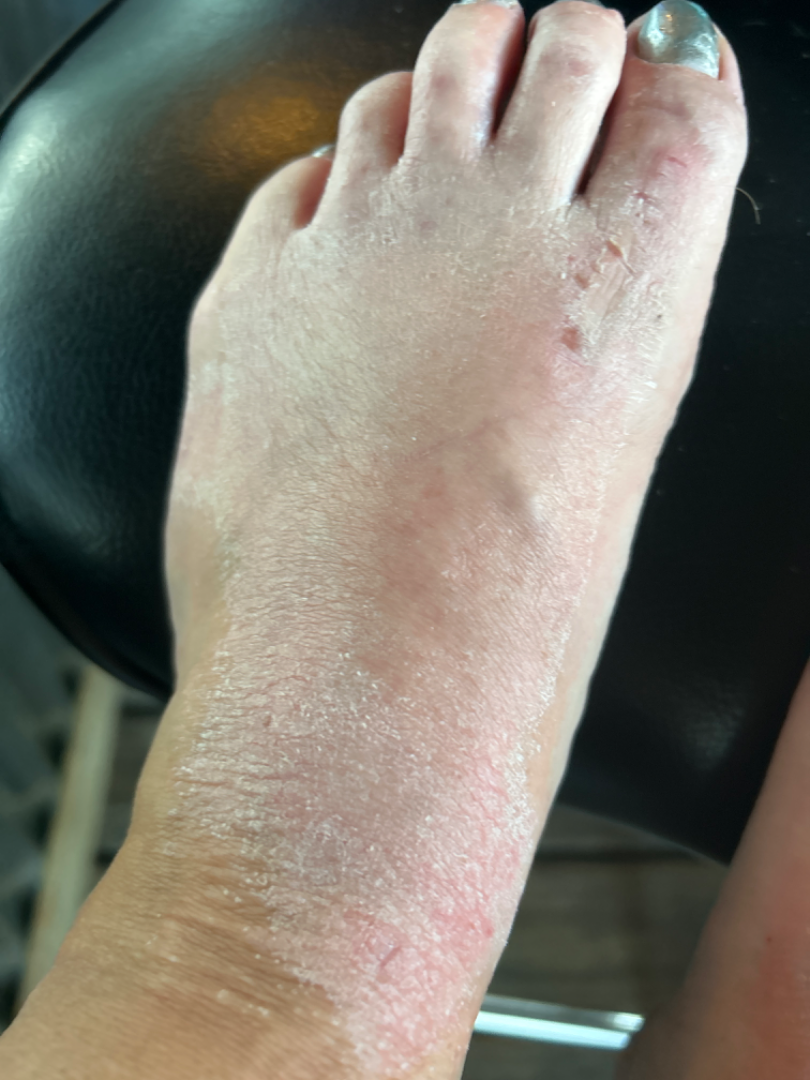photo taken = close-up
present for = one to four weeks
site = leg, top or side of the foot and arm
symptoms = itching and bothersome appearance
patient's own categorization = a rash
described texture = rough or flaky, raised or bumpy and flat
patient = female, age 30–39
impression = the leading consideration is Allergic Contact Dermatitis; also raised was Lichen Simplex Chronicus; possibly Psoriasis